A dermoscopic close-up of a skin lesion.
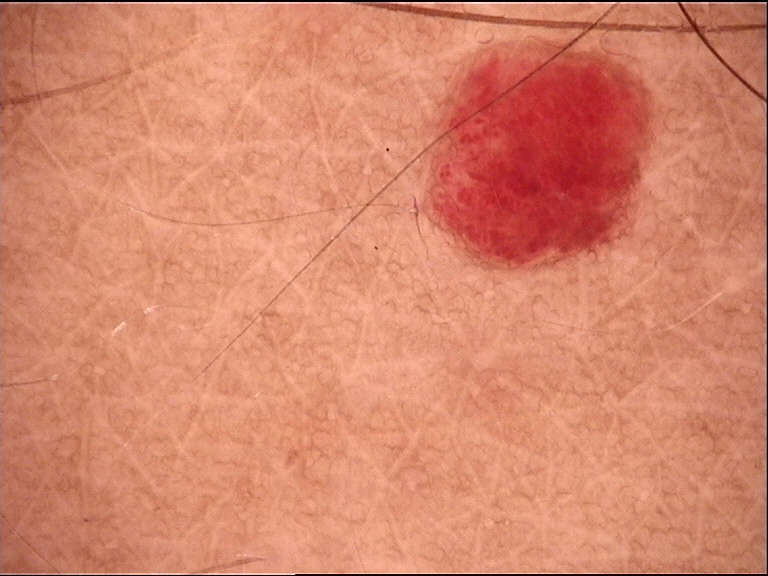This is a vascular lesion. Classified as a hemangioma.